The subject is a male aged 30–39 · the arm is involved · the patient described the issue as a rash · no constitutional symptoms were reported · the condition has been present for one to four weeks · symptoms reported: bothersome appearance, itching and burning · the photograph was taken at an angle · Fitzpatrick skin type II; lay reviewers estimated Monk Skin Tone 1 or 2 · the patient notes the lesion is raised or bumpy and rough or flaky — 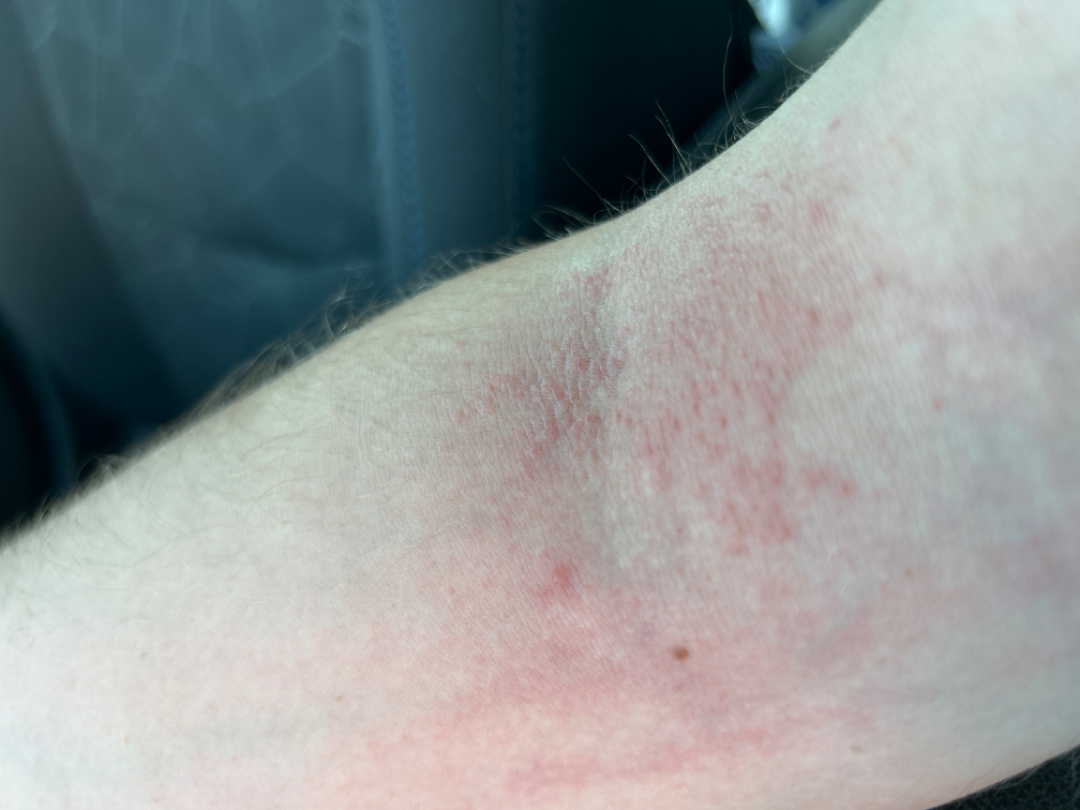diagnostic considerations: in keeping with Eczema.